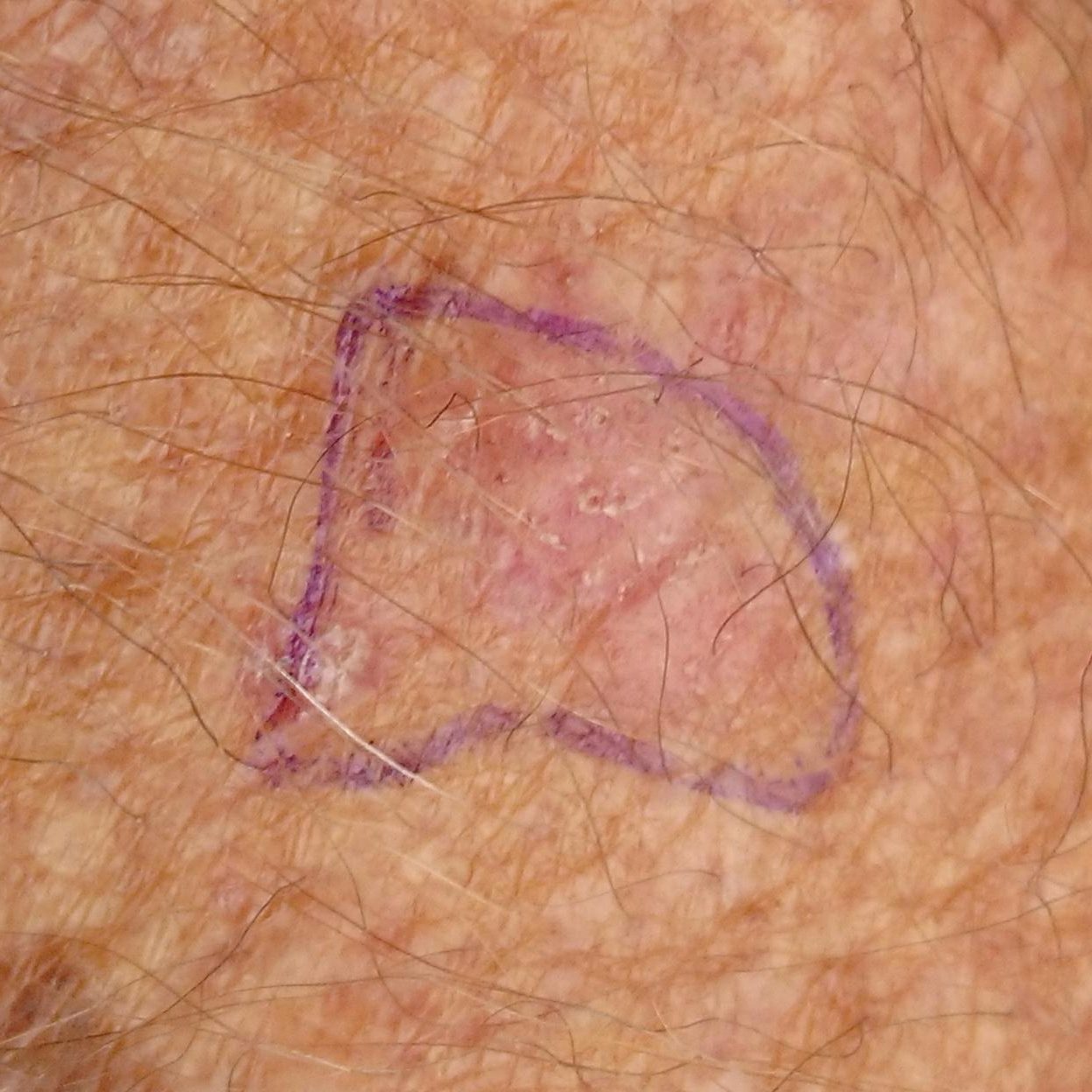A patient age 71.
A clinical photo of a skin lesion taken with a smartphone.
The lesion involves a forearm.
Per patient report, the lesion itches.
Diagnosed by dermatologist consensus as an actinic keratosis.